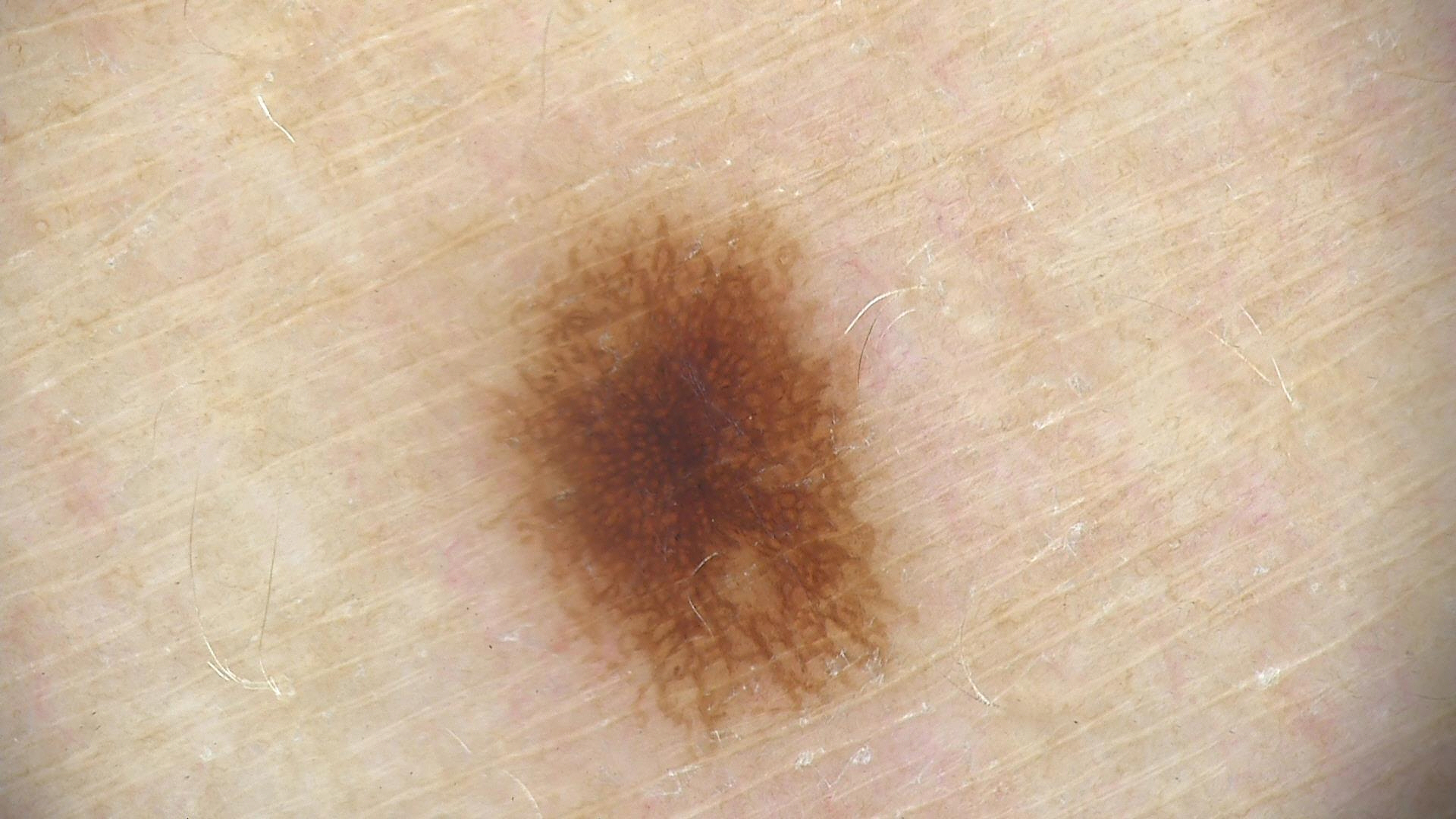| feature | finding |
|---|---|
| diagnosis | dysplastic junctional nevus (expert consensus) |